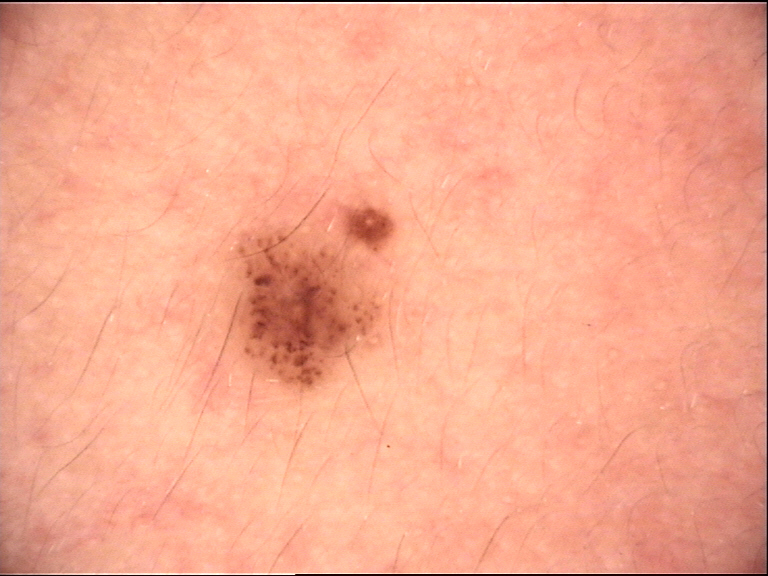Impression:
The diagnosis was a benign lesion — a dysplastic junctional nevus.